The affected area is the head or neck. The photograph was taken at an angle. No associated systemic symptoms reported.
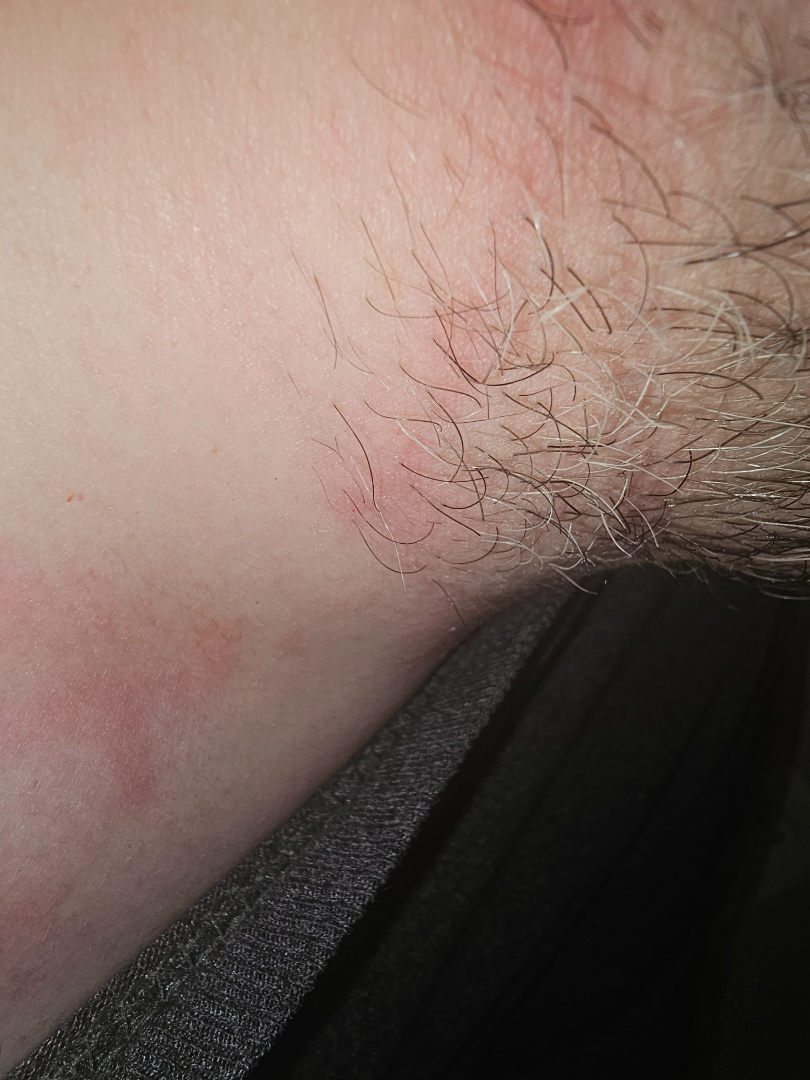Findings: A single dermatologist reviewed the case: Tinea, Pityriasis rosea and Allergic Contact Dermatitis were each considered, in no particular order.